A dermatoscopic image of a skin lesion.
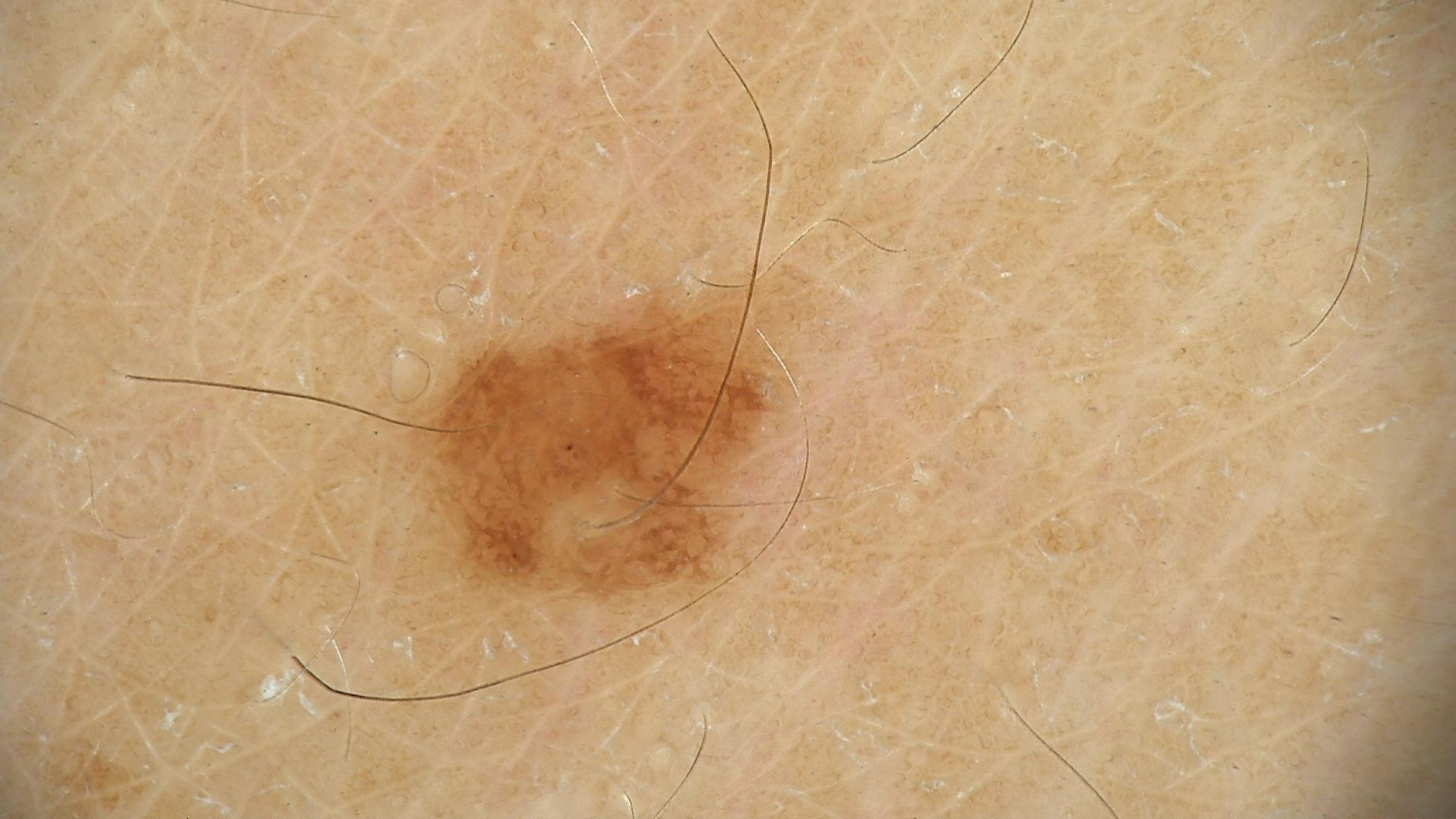label: dysplastic junctional nevus (expert consensus).